A clinical close-up of a skin lesion · acquired for a research image collection, with no referral diagnosis · a female subject 48 years of age: 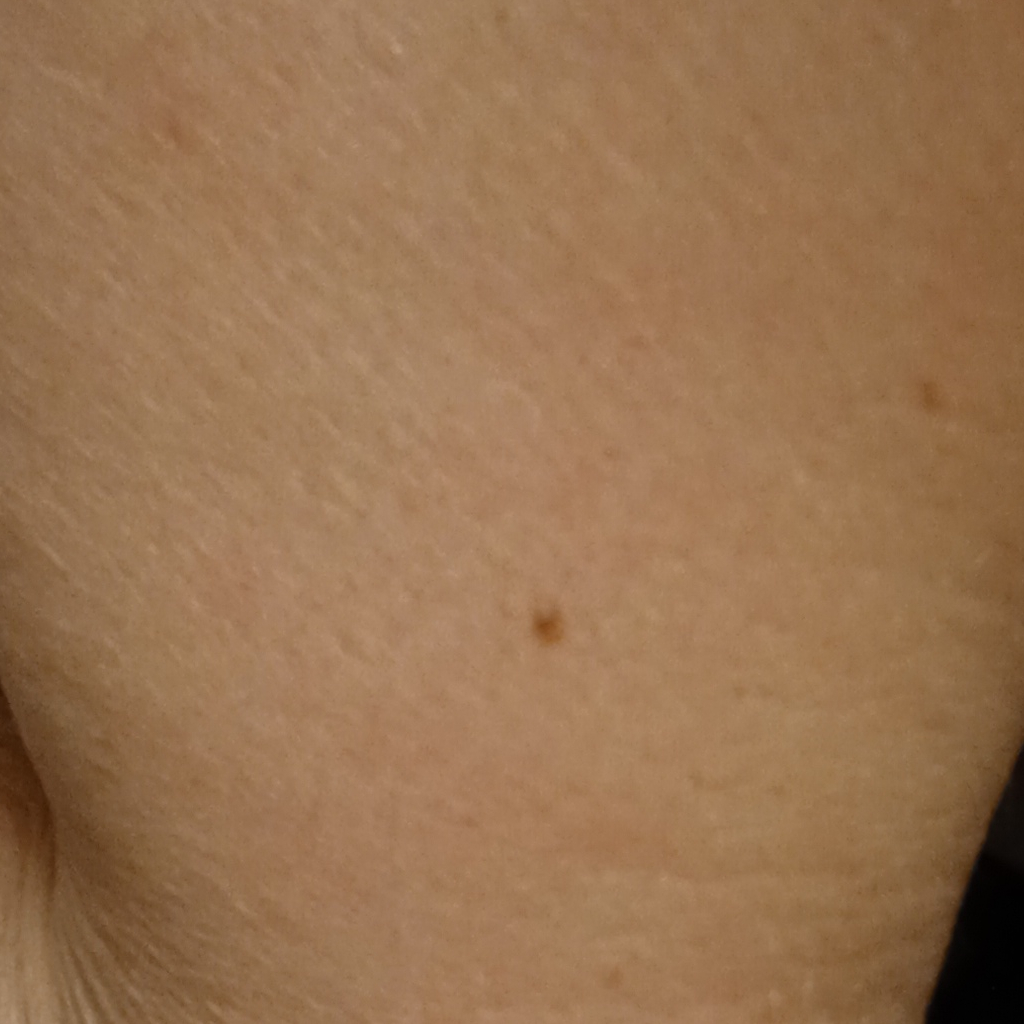Findings: The lesion is on an arm. The lesion is about 2.7 mm across. Assessment: The diagnostic impression was a melanocytic nevus.